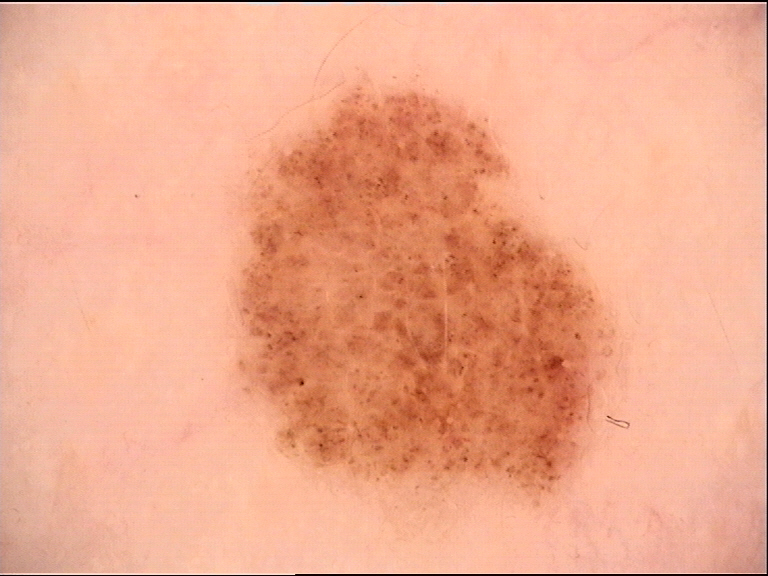| field | value |
|---|---|
| assessment | junctional nevus (expert consensus) |